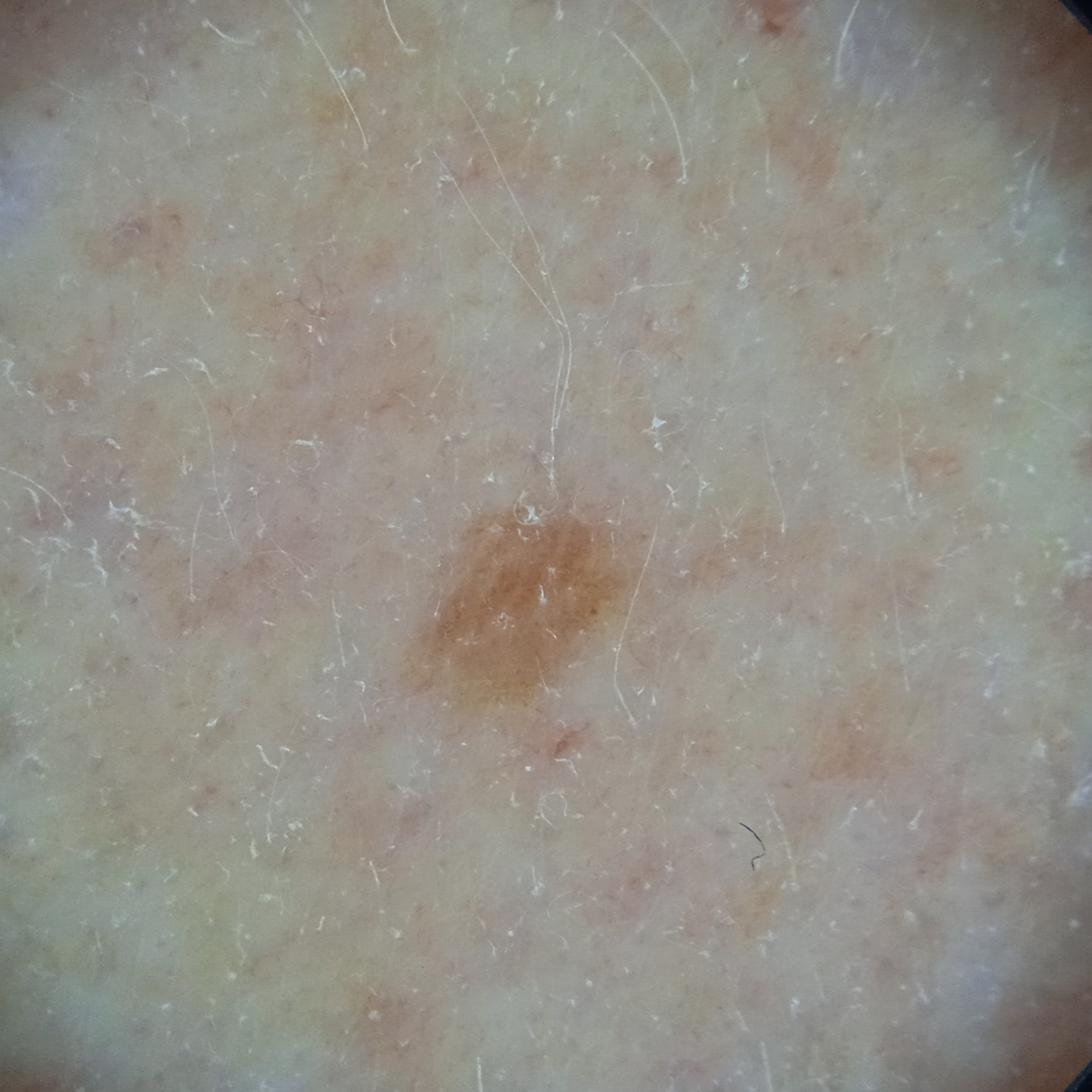Case summary:
A female patient 92 years of age. A dermatoscopic image of a skin lesion. The lesion involves the face.
Conclusion:
Four dermatologists reviewed the lesion; the consensus was a melanocytic nevus; diagnostic confidence was good.